A dermoscopic image of a skin lesion:
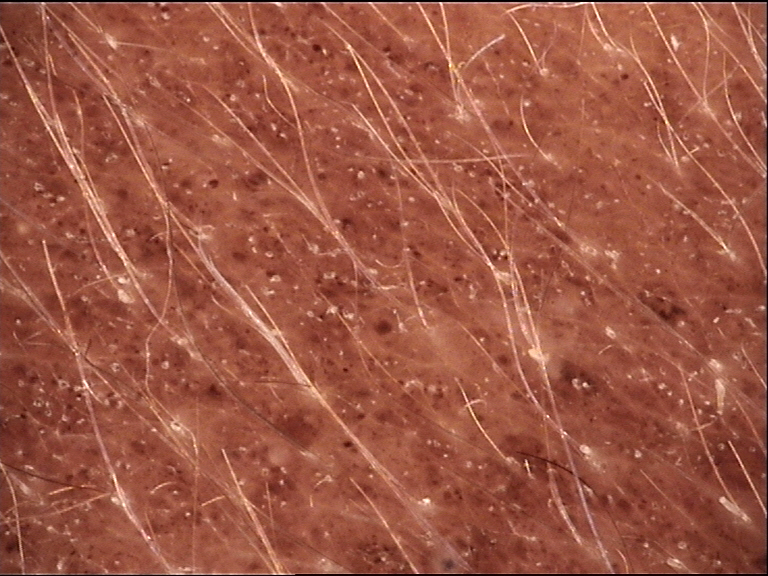{"lesion_type": {"main_class": "banal", "pattern": "compound"}, "diagnosis": {"name": "congenital compound nevus", "code": "ccb", "malignancy": "benign", "super_class": "melanocytic", "confirmation": "expert consensus"}}